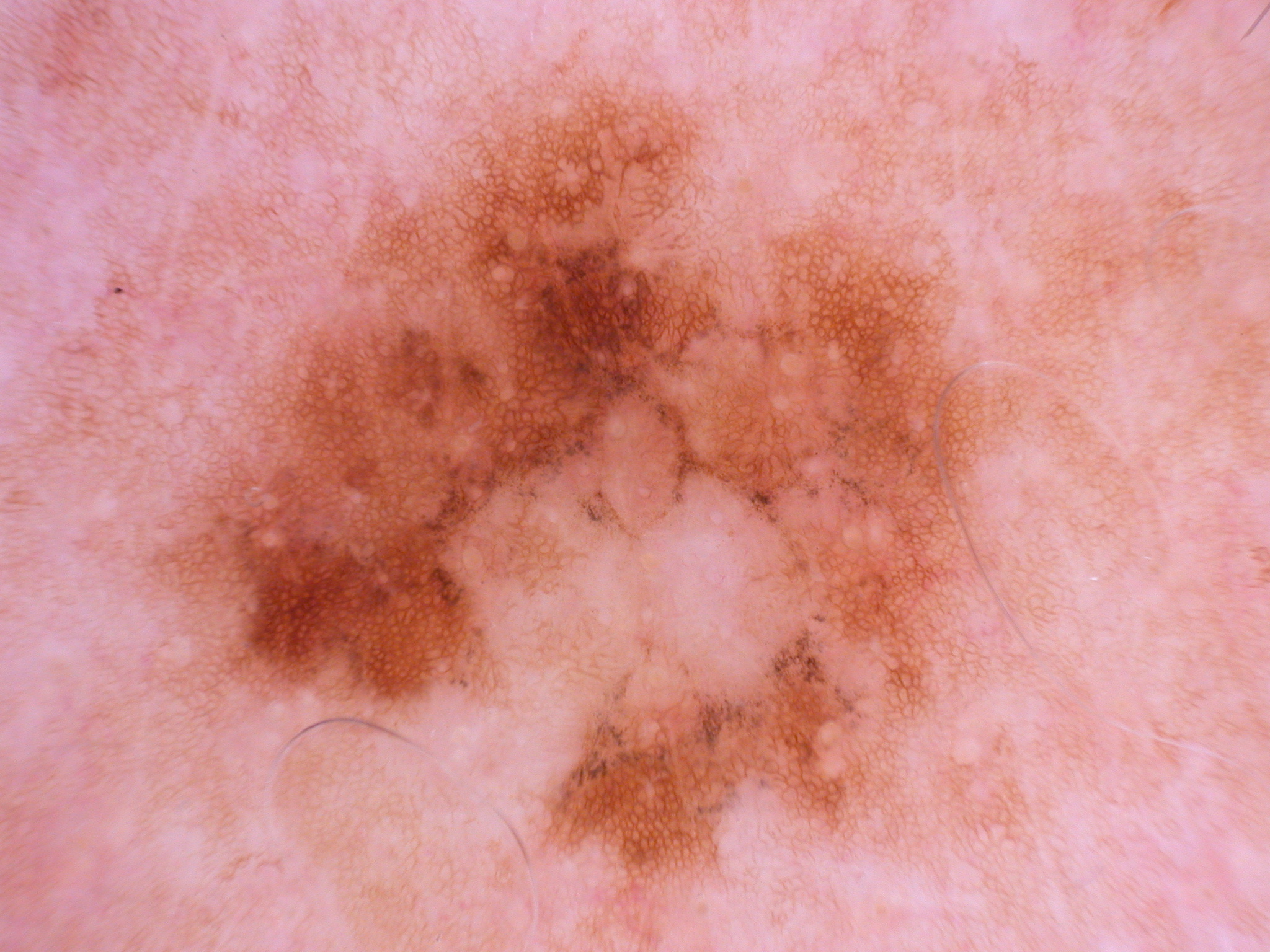A dermoscopic close-up of a skin lesion. As (left, top, right, bottom), the lesion spans 142, 82, 1039, 945. Dermoscopy demonstrates pigment network; no globules, milia-like cysts, streaks, or negative network. Clinically diagnosed as a melanocytic nevus, a benign lesion.